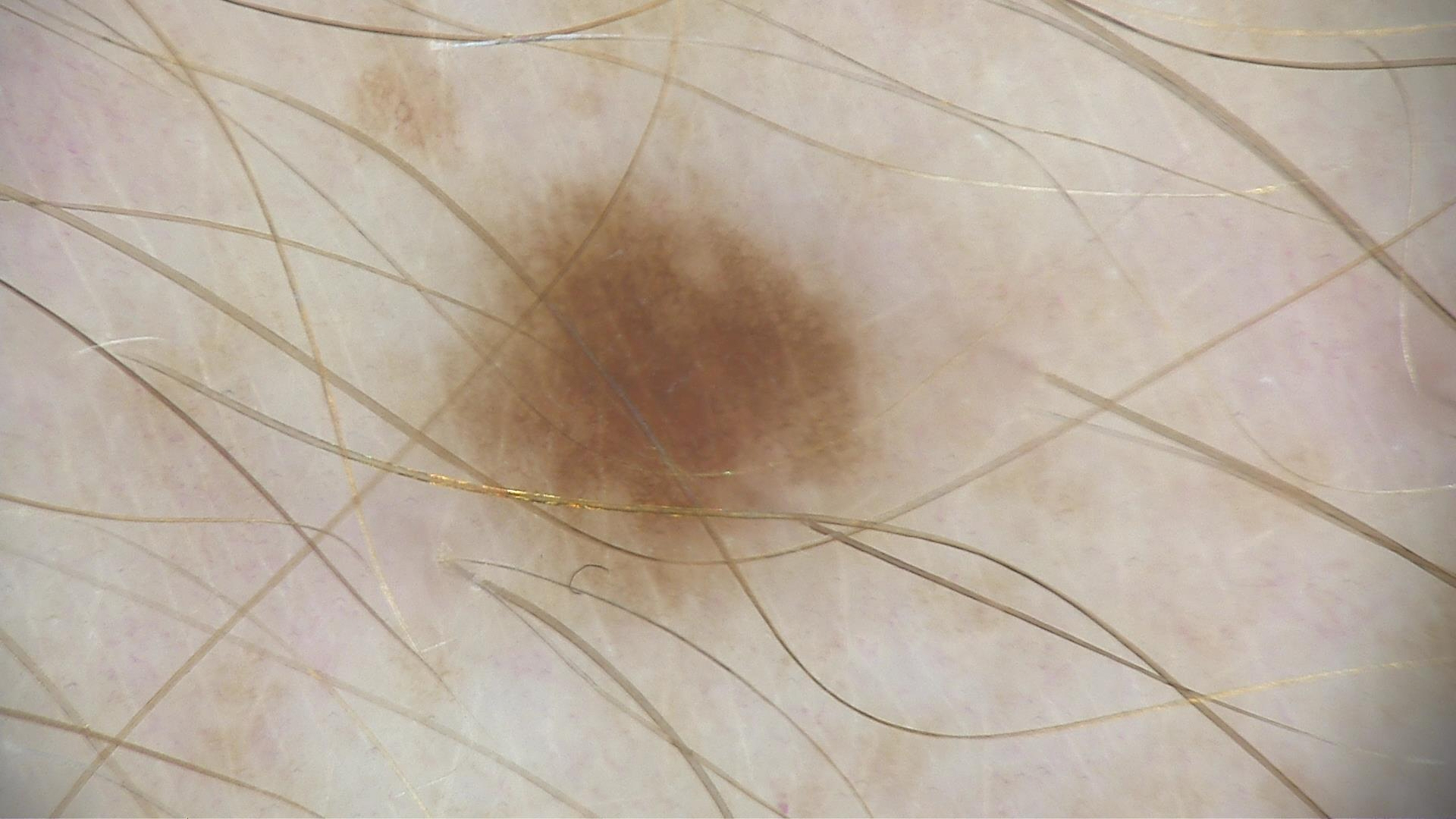Q: What was the diagnostic impression?
A: dysplastic junctional nevus (expert consensus)